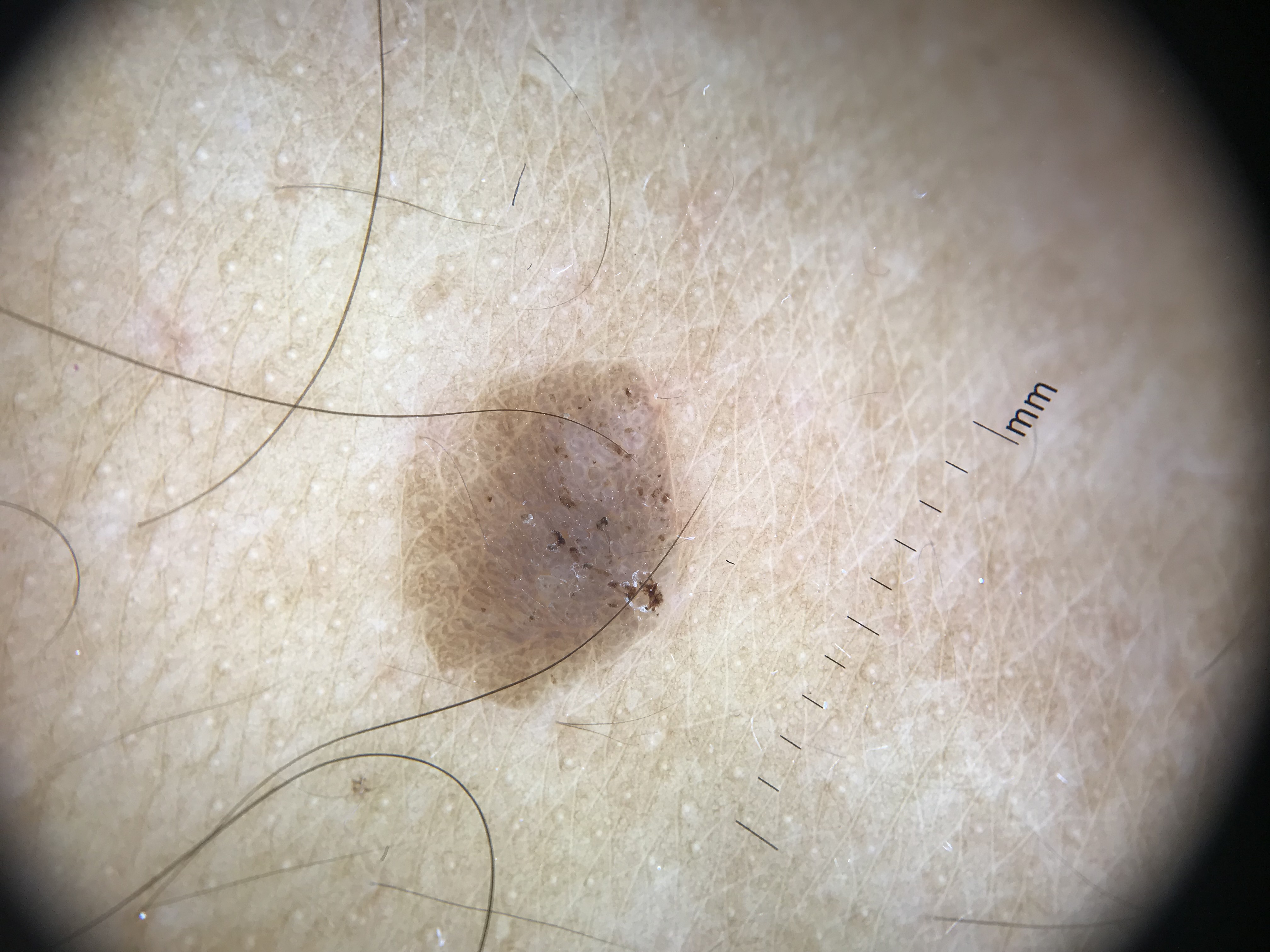The morphology is that of a keratinocytic lesion.
Diagnosed as a seborrheic keratosis.